The photograph is a close-up of the affected area. The subject is 18–29, female. The lesion involves the arm — 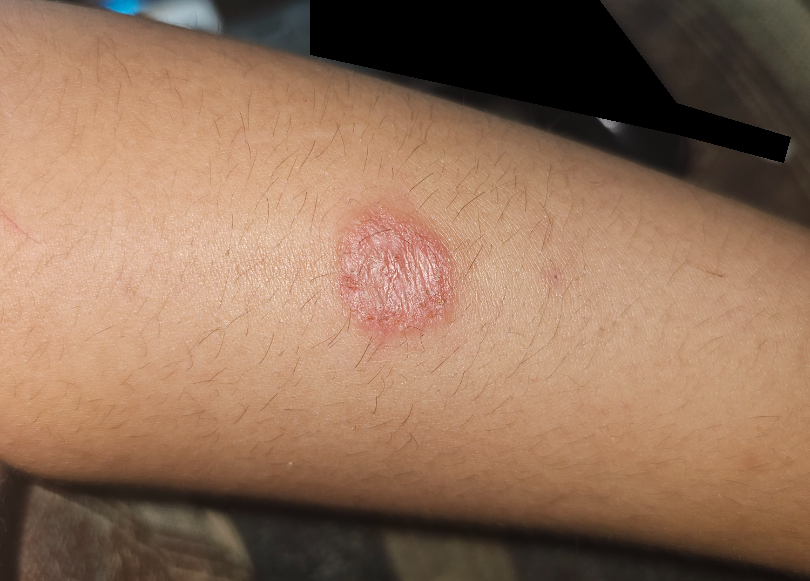Eczema (favored); Psoriasis (remote); Tinea (remote); Deep fungal infection (remote); Cutaneous sarcoidosis (remote); Skin and soft tissue atypical mycobacterial infection (remote).